A female subject approximately 45 years of age · a dermoscopy image of a single skin lesion.
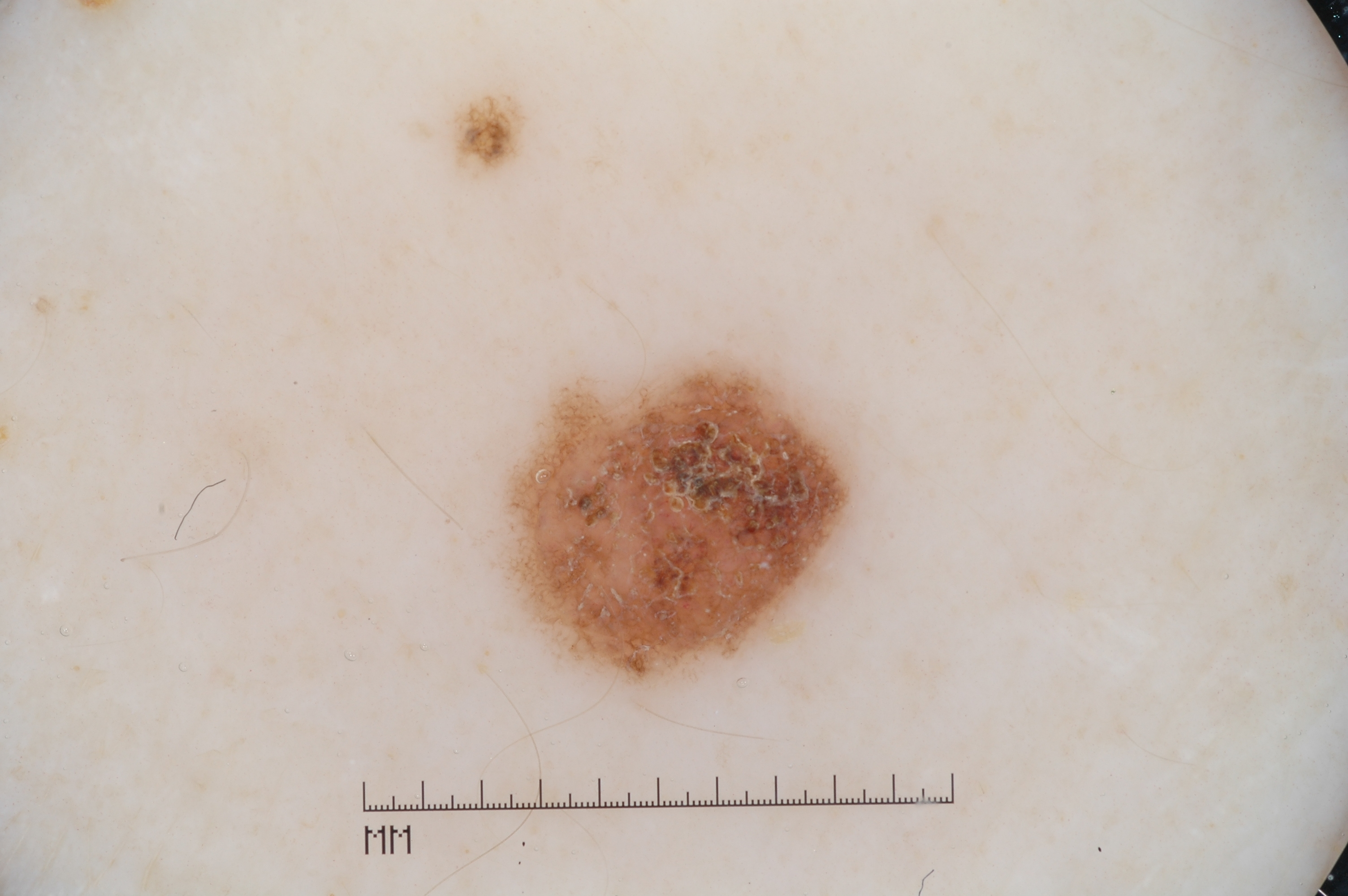The lesion is located at x1=506, y1=364, x2=853, y2=686.
Dermoscopically, the lesion shows pigment network, with no milia-like cysts, negative network, or streaks.
Consistent with a melanocytic nevus, a benign skin lesion.